A dermoscopic image of a skin lesion.
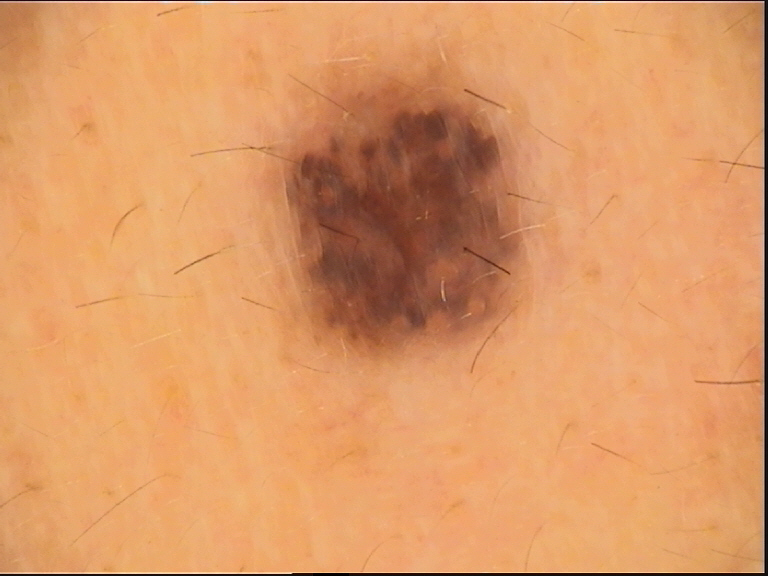Consistent with a dysplastic compound nevus.